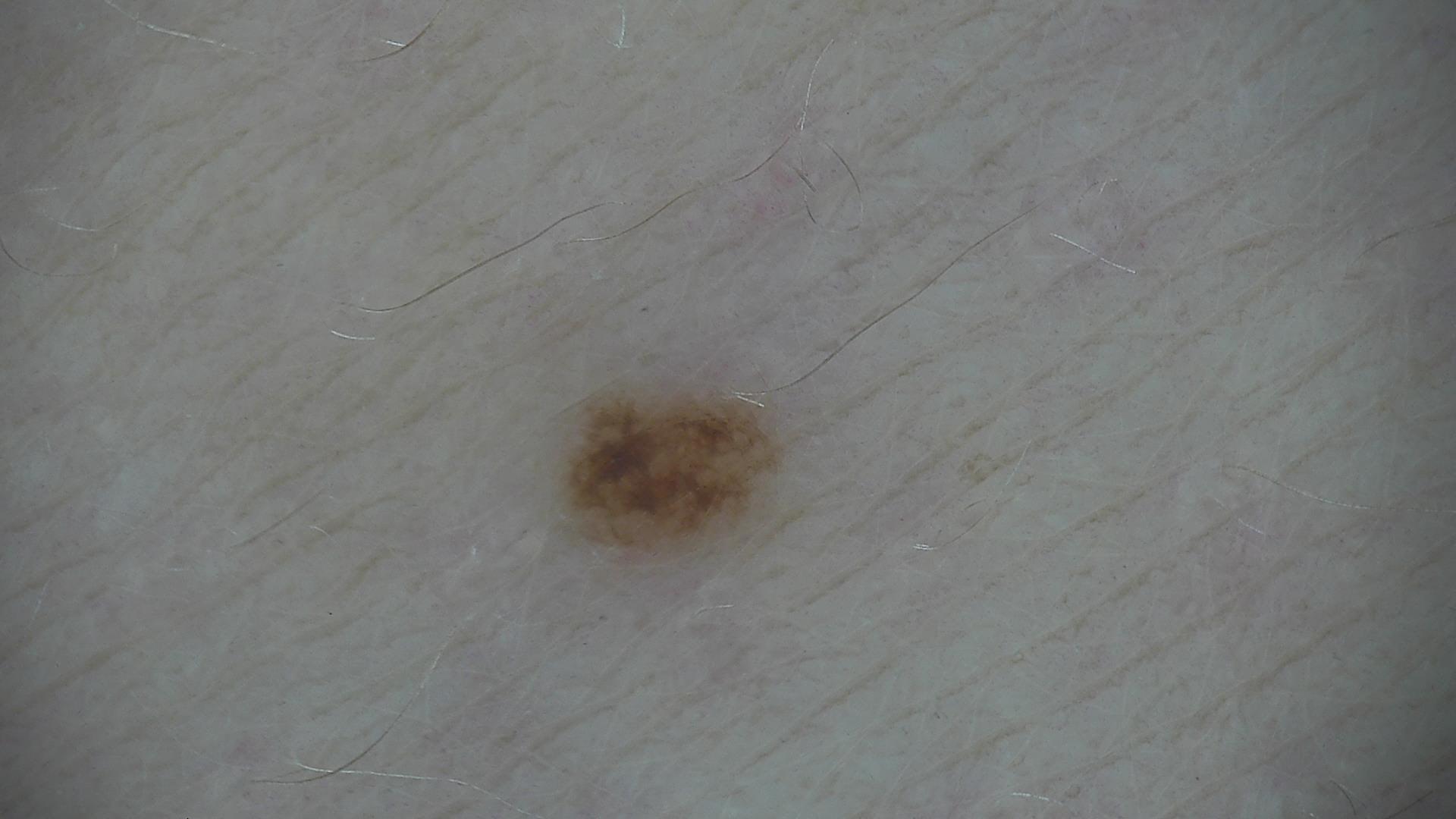image: dermatoscopy | class: acral compound nevus (expert consensus).